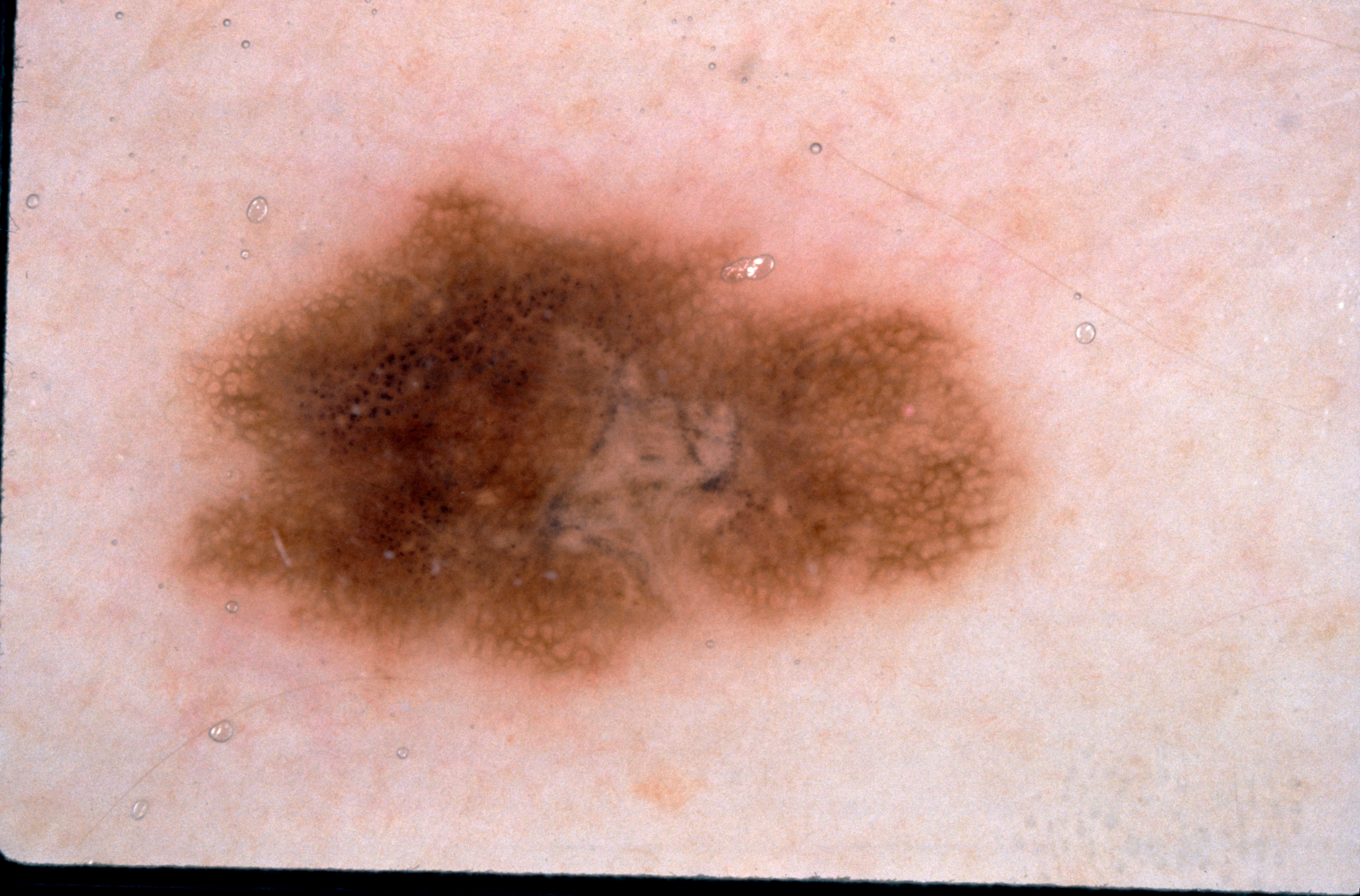Dermoscopy of a skin lesion. With coordinates (x1, y1, x2, y2), the lesion is located at 168/166/1030/699. Clinically diagnosed as a melanocytic nevus, a benign lesion.